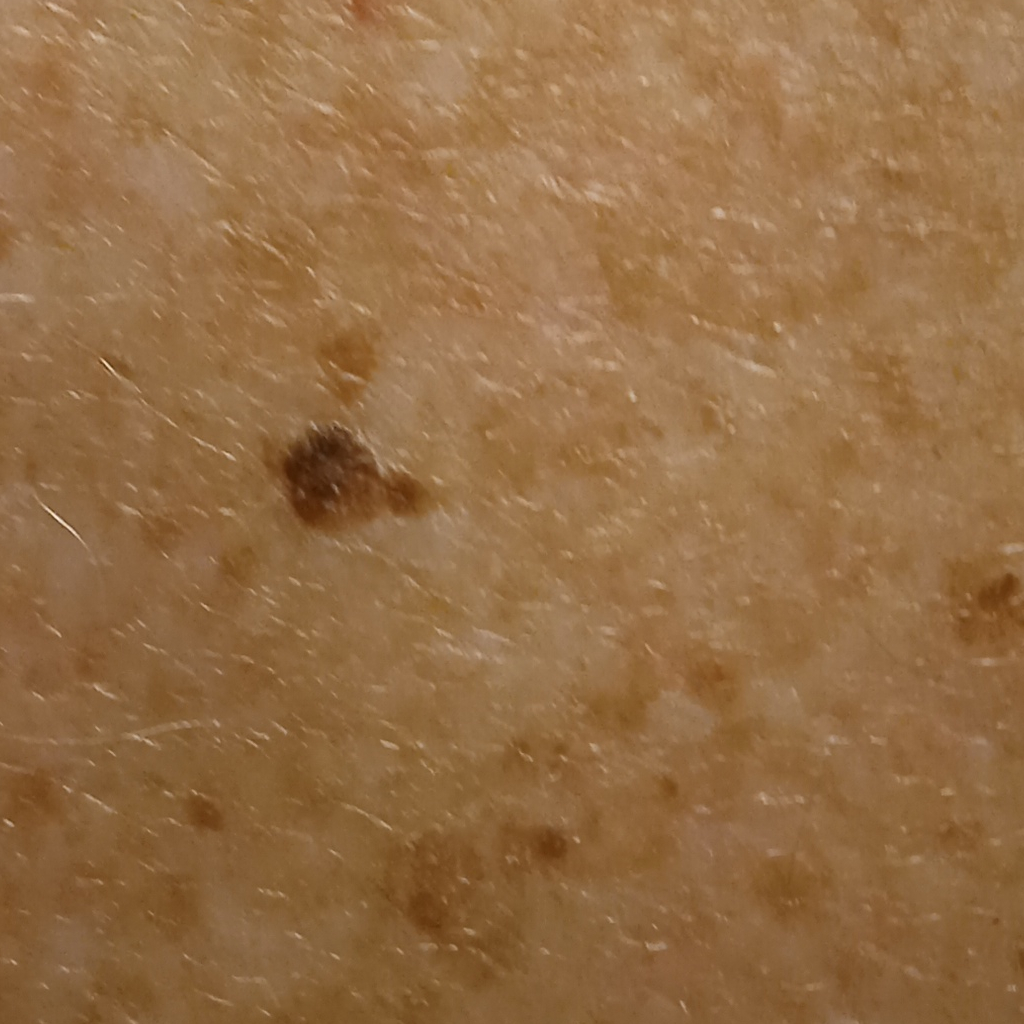{"lesion_location": "the back", "lesion_size": {"diameter_mm": 5.5}, "diagnosis": {"name": "seborrheic keratosis", "malignancy": "benign"}}